A male subject, in their mid-50s · a dermoscopy image of a single skin lesion: 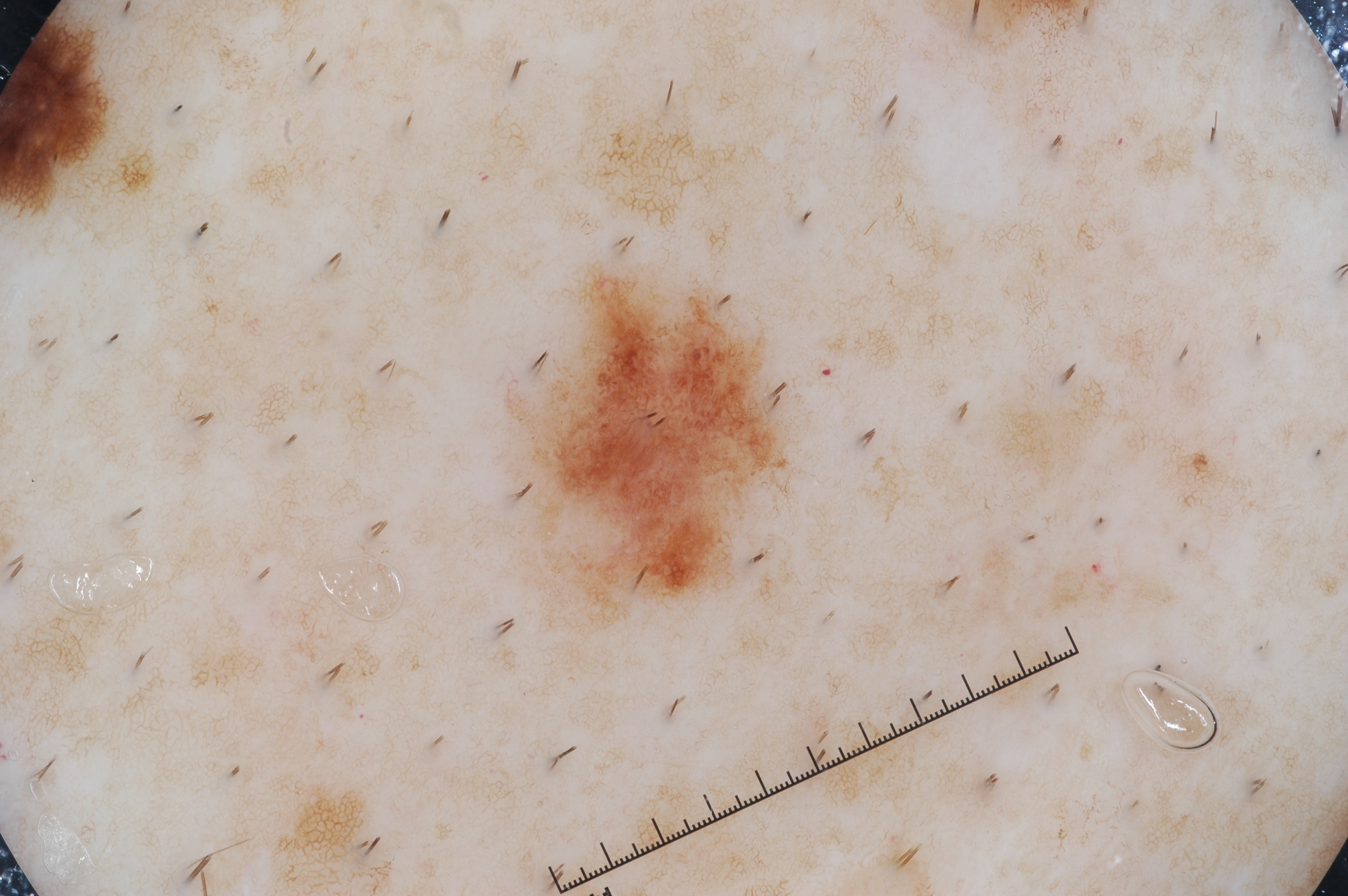{"lesion_extent": "small", "dermoscopic_features": {"present": ["pigment network", "milia-like cysts"], "absent": ["streaks", "negative network"]}, "lesion_location": {"bbox_xyxy": [527, 280, 779, 602]}, "diagnosis": {"name": "melanocytic nevus", "malignancy": "benign", "lineage": "melanocytic", "provenance": "clinical"}}